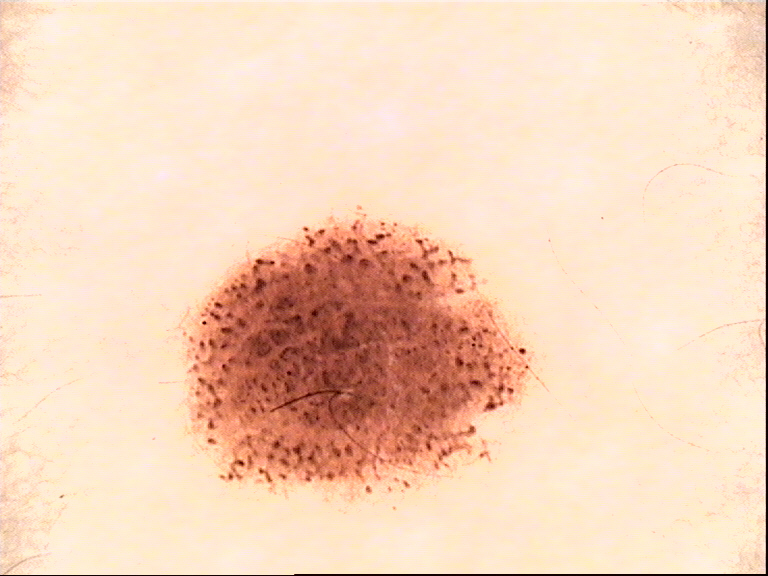imaging=dermatoscopy | class=compound nevus (expert consensus).